A skin lesion imaged with a dermatoscope.
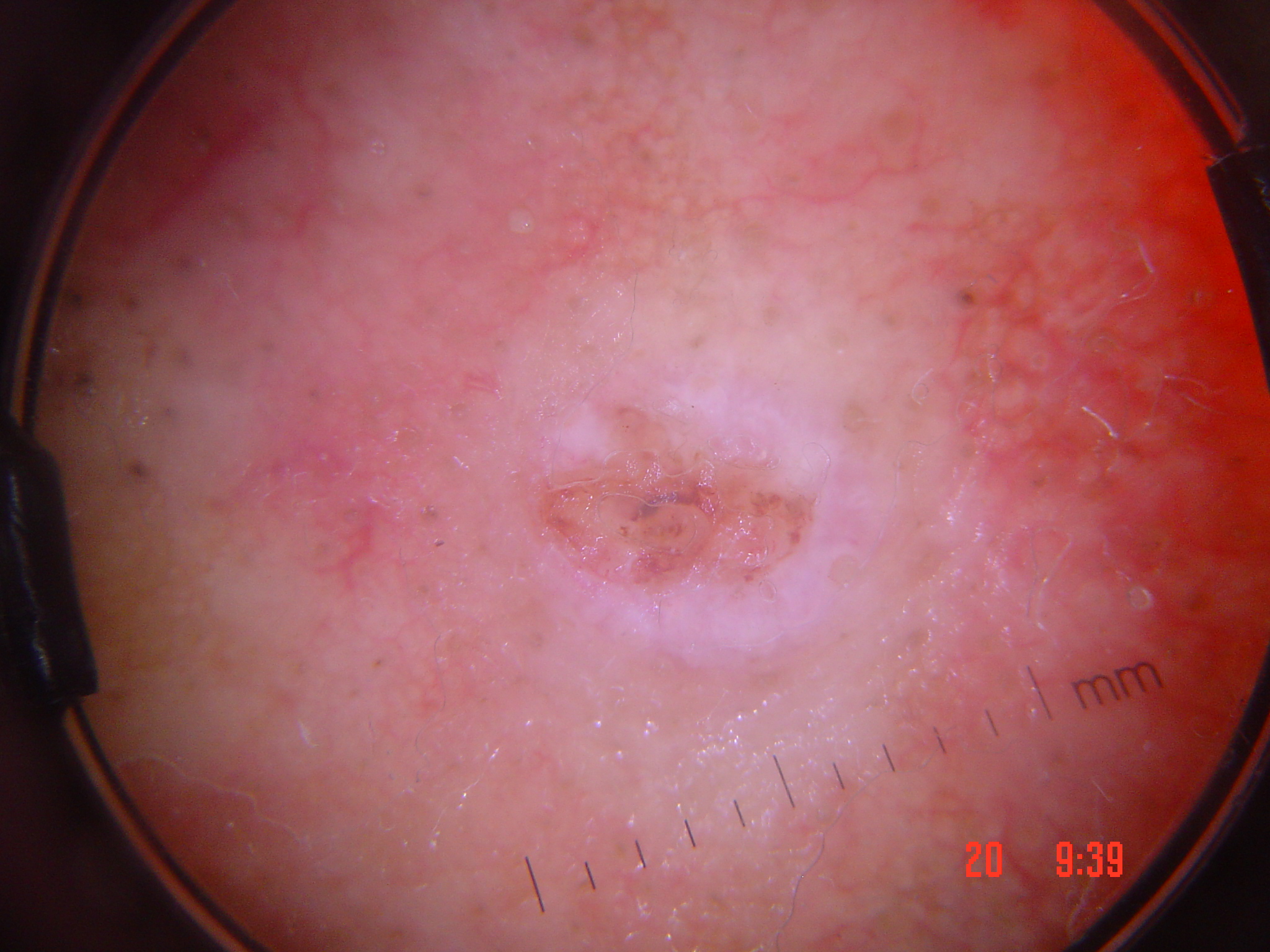Q: How is the lesion classified?
A: keratinocytic
Q: What did the workup show?
A: squamous cell carcinoma (biopsy-proven)